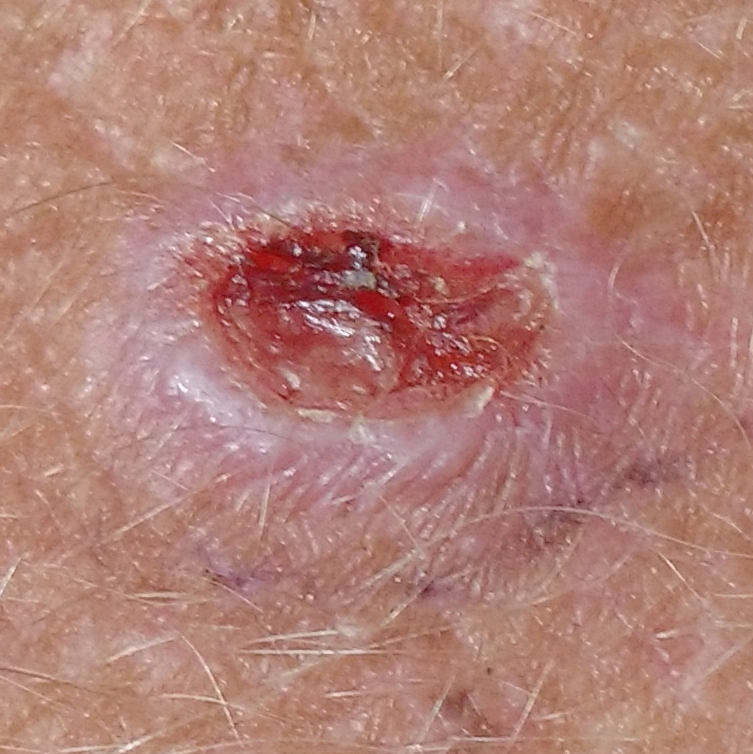The chart records prior skin cancer (patient or family) and pesticide exposure.
The patient was assessed as FST II.
A male patient 50 years of age.
A smartphone photograph of a skin lesion.
The lesion is located on the neck.
The lesion measures 15 × 10 mm.
The patient reports that the lesion itches, is elevated, hurts, and has bled.
Histopathology confirmed a malignancy — a basal cell carcinoma.